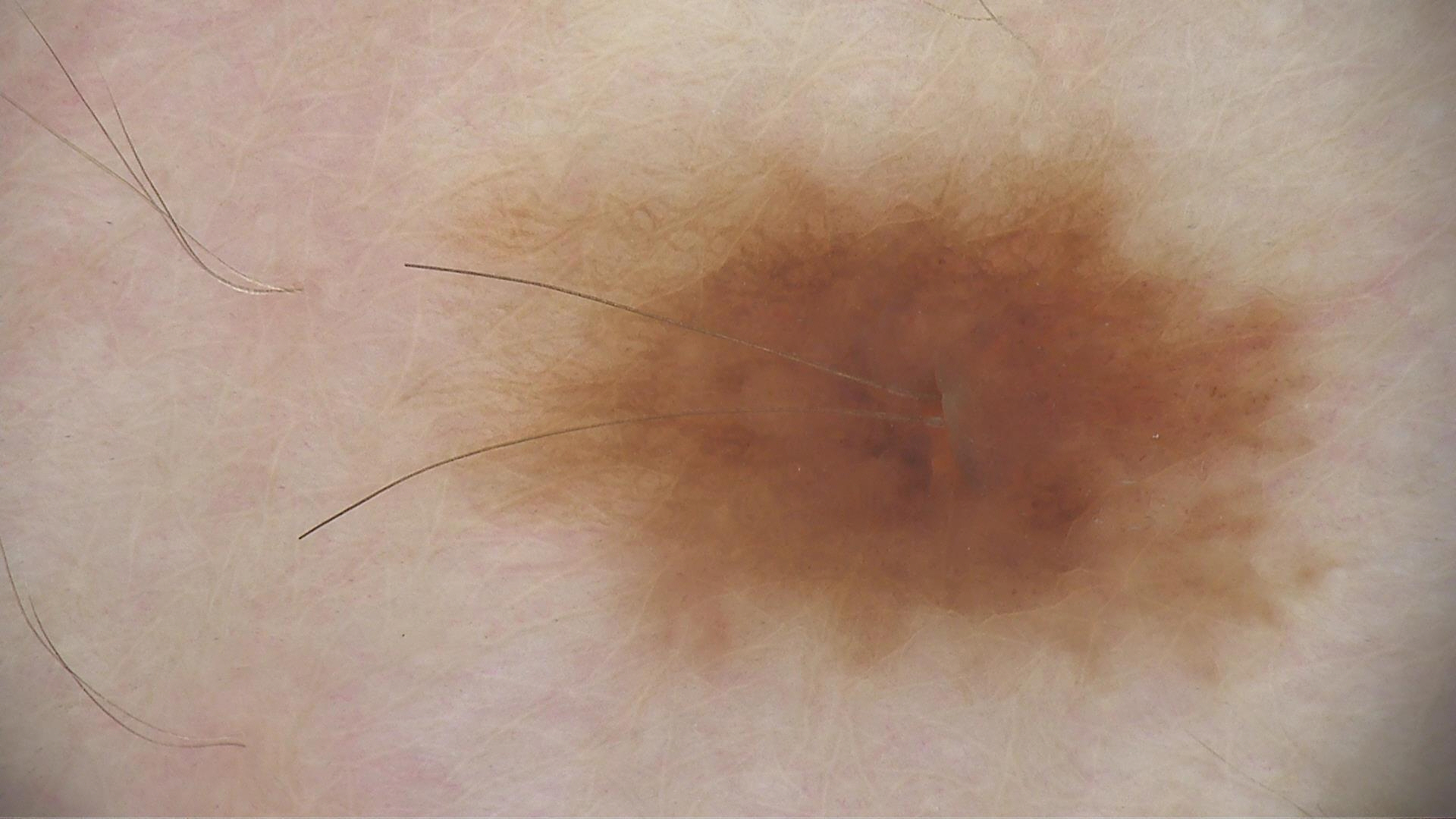Case:
- imaging — dermoscopy
- assessment — dysplastic compound nevus (expert consensus)